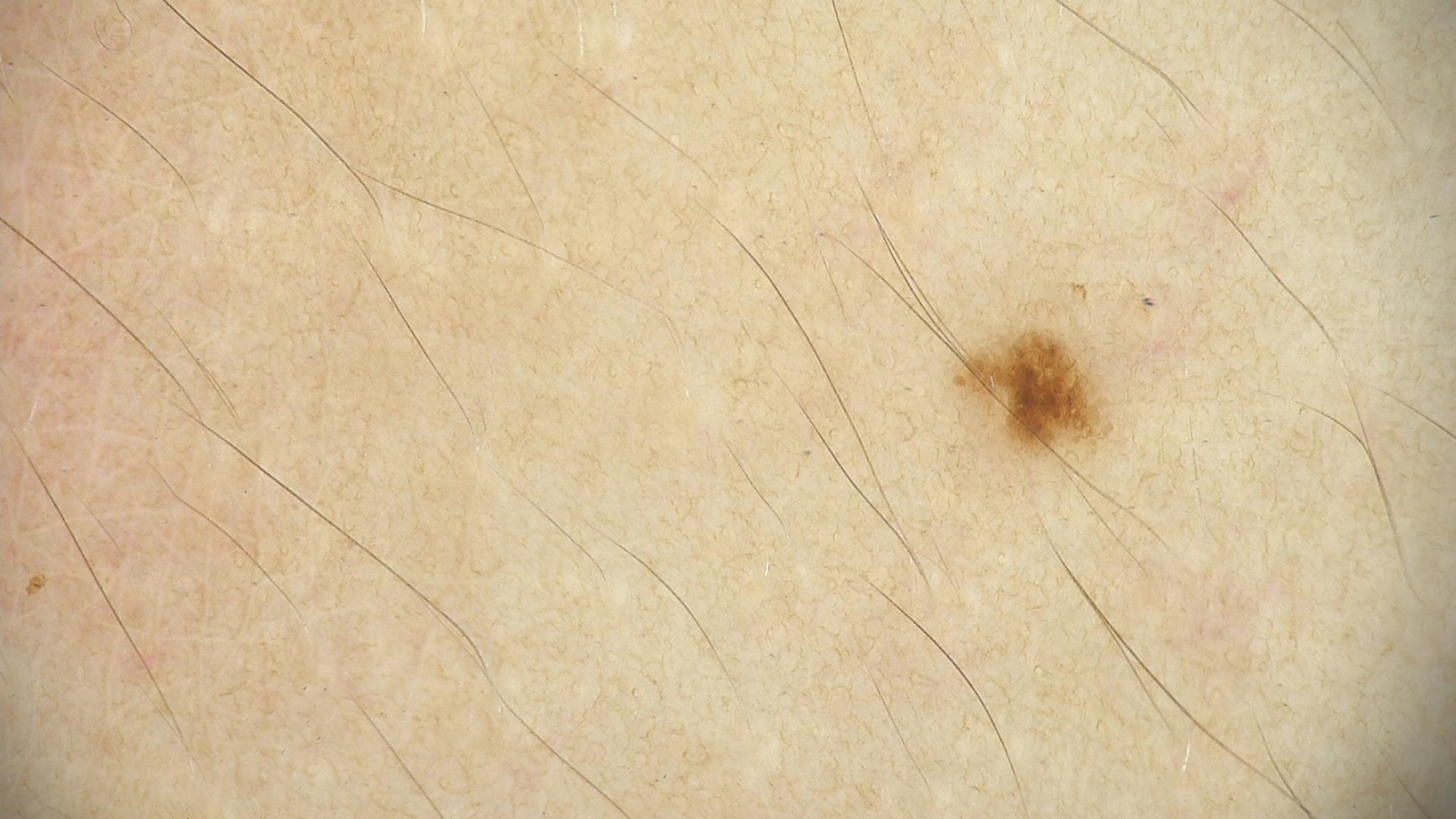| field | value |
|---|---|
| image type | dermoscopy |
| diagnostic label | dysplastic junctional nevus (expert consensus) |